A dermoscopic close-up of a skin lesion.
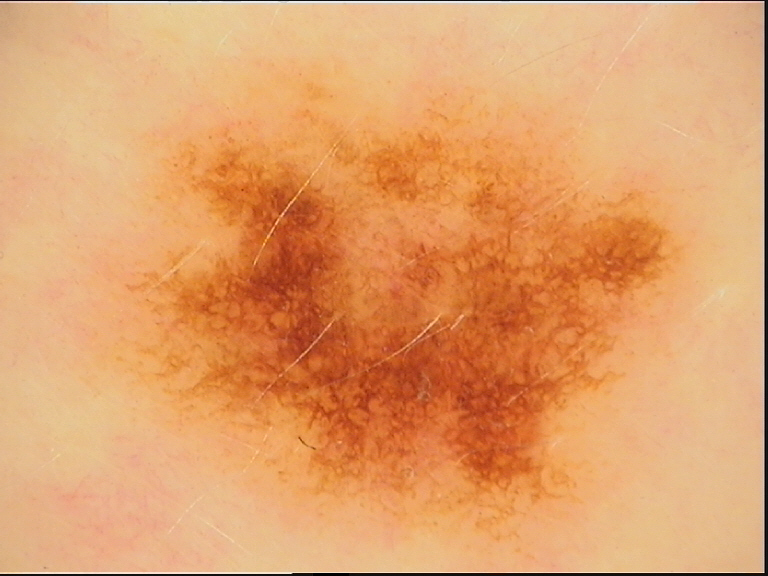Conclusion: Consistent with a benign lesion — a dysplastic junctional nevus.